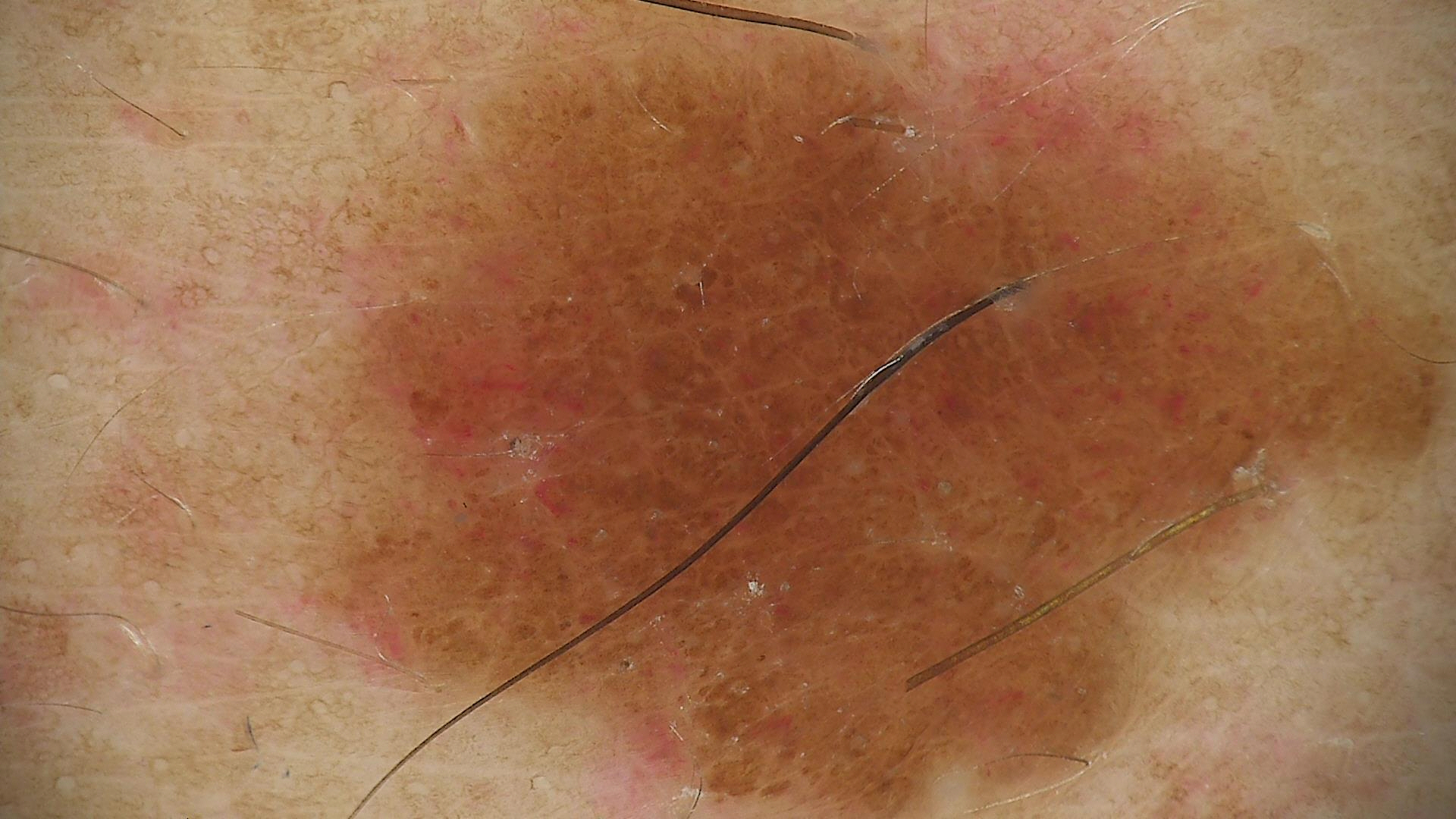Diagnosed as a compound nevus.